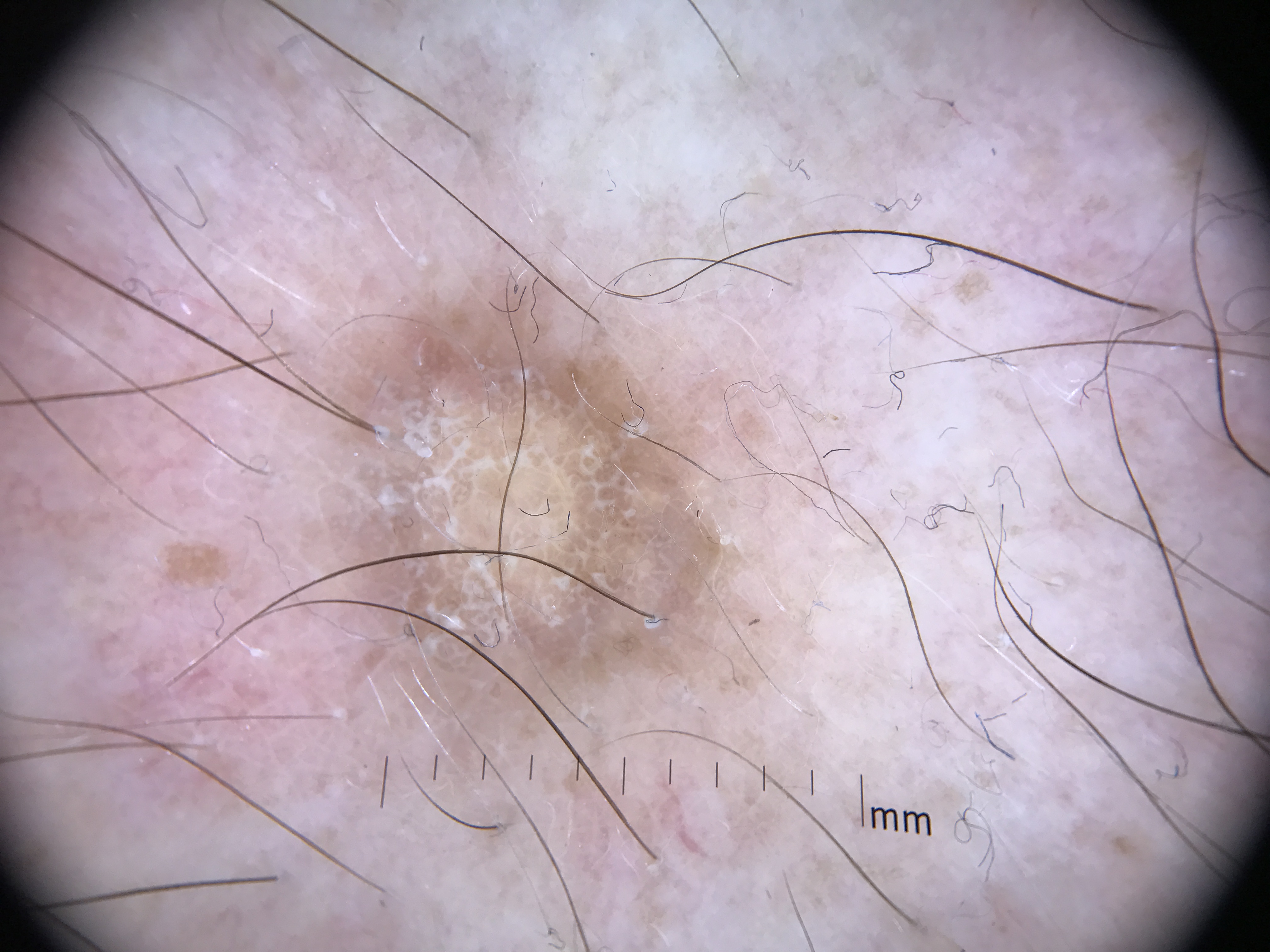| key | value |
|---|---|
| label | dermatofibroma (expert consensus) |